Symptoms reported: itching, burning, enlargement and bothersome appearance · the patient is male · the photograph was taken at an angle · the lesion involves the leg and arm · texture is reported as rough or flaky and flat — 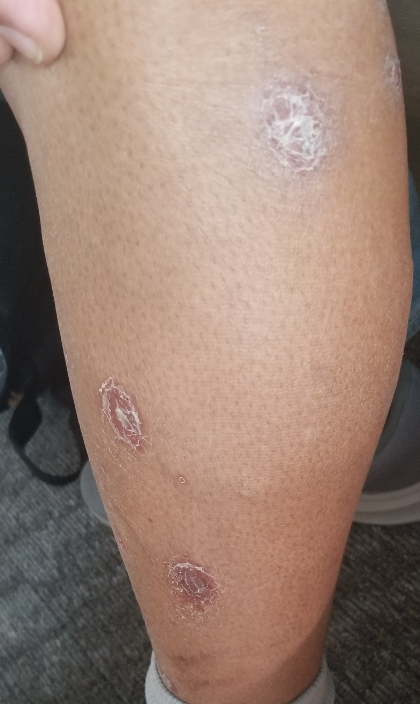impression = the leading consideration is Psoriasis; the differential also includes Eczema; less likely is Syphilis.